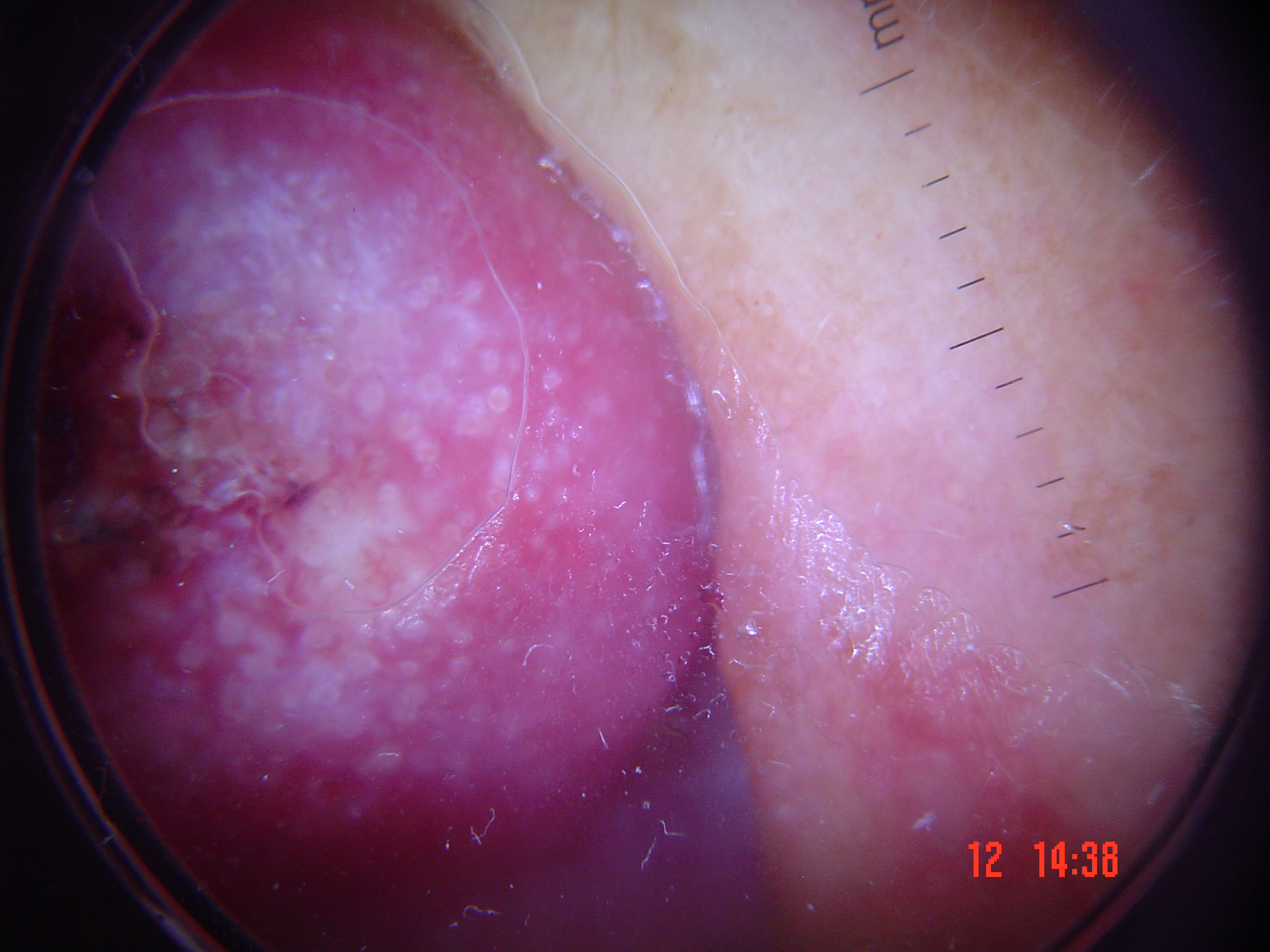Biopsy-confirmed as a keratinocytic lesion — a squamous cell carcinoma.